A dermoscopic close-up of a skin lesion.
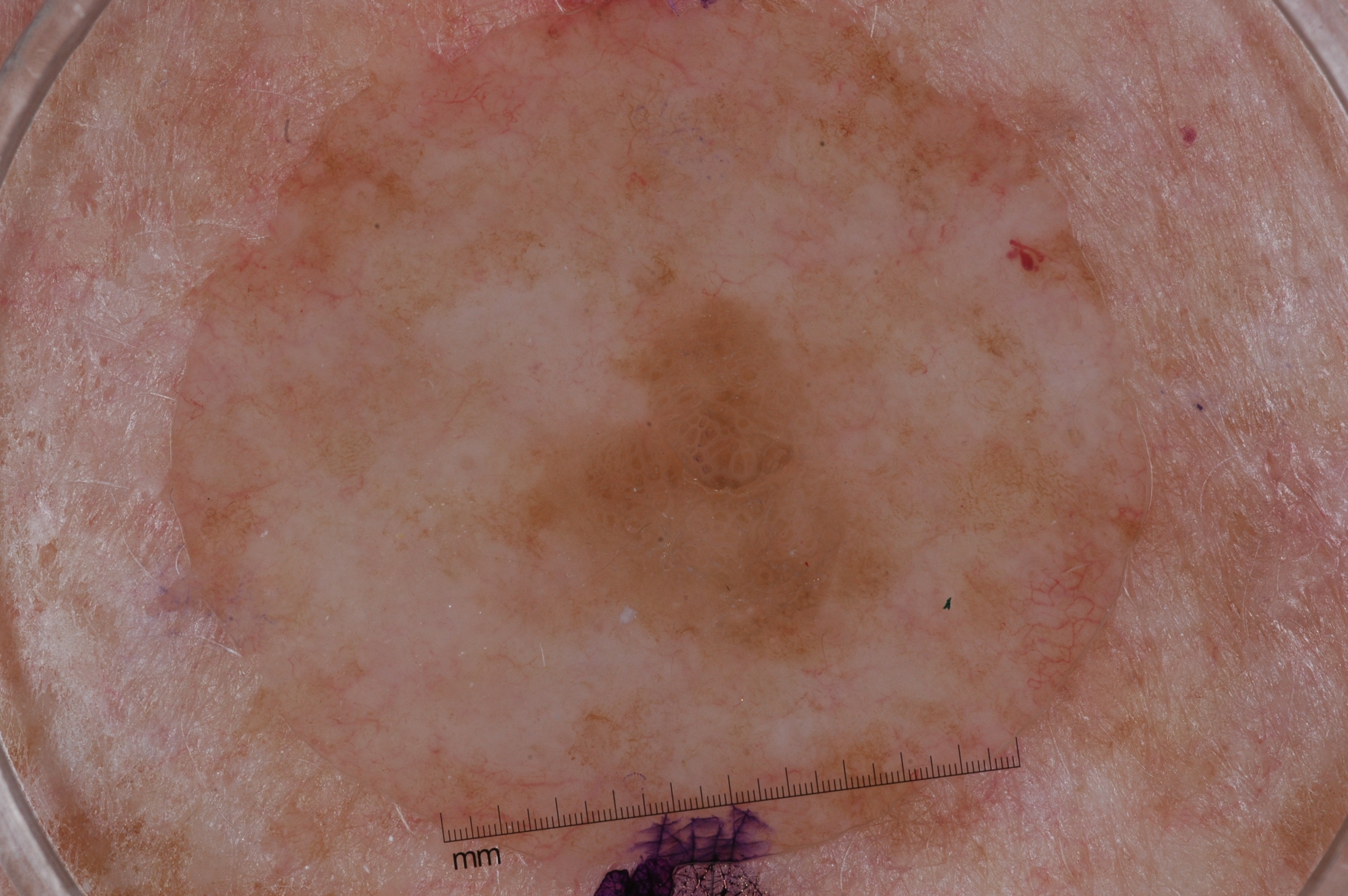dermoscopic pattern: milia-like cysts; bounding box: [529, 296, 910, 663]; diagnostic label: a seborrheic keratosis.